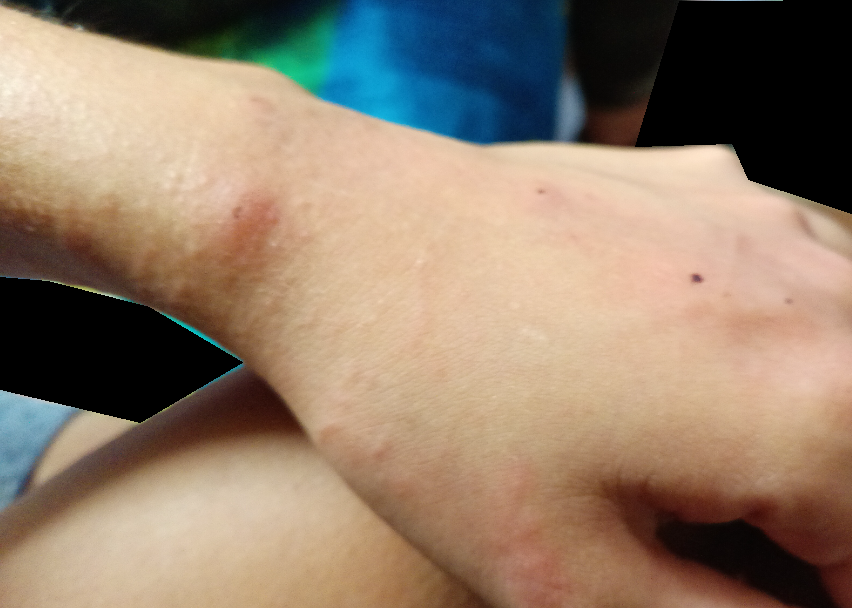The skin findings could not be characterized from the image.
Reported lesion symptoms include itching.
This image was taken at an angle.
The lesion involves the arm and head or neck.
Texture is reported as raised or bumpy.